The contributor reports the condition has been present for three to twelve months; the patient also reports joint pain and fatigue; the patient considered this a rash; this is a close-up image; the lesion involves the back of the hand; the lesion is associated with pain, itching, darkening and burning; non-clinician graders estimated 2 on the Monk skin tone scale; the contributor reports the lesion is rough or flaky.
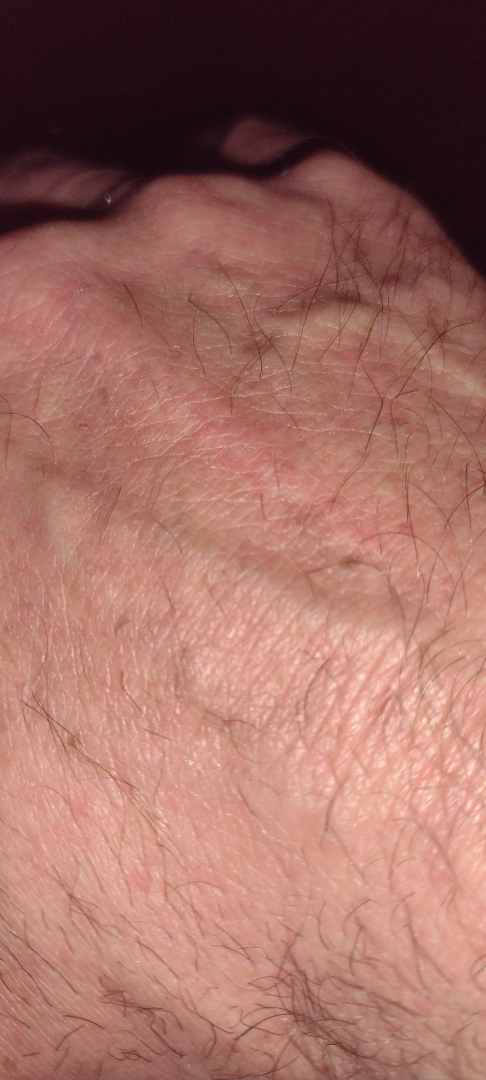Impression: No skin condition was discernible on photographic review.